Dermoscopy of a skin lesion: 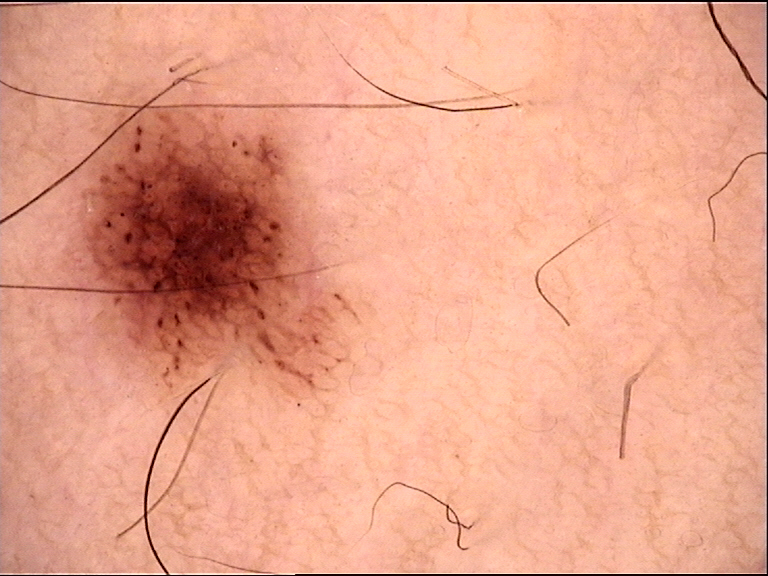Q: What is the diagnosis?
A: dysplastic junctional nevus (expert consensus)